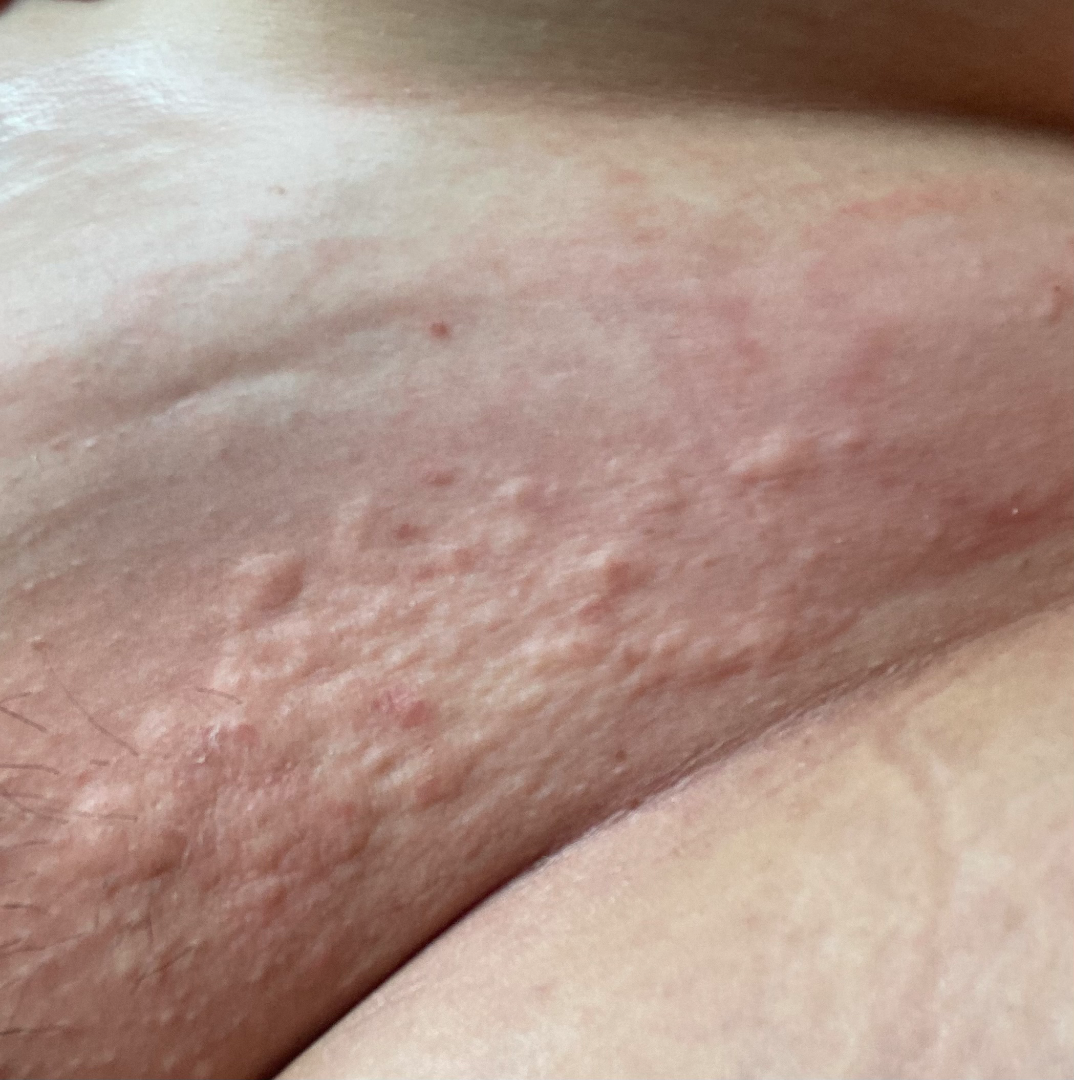The condition could not be reliably identified from the image. Texture is reported as raised or bumpy. Self-categorized by the patient as a rash. The patient reports enlargement and itching. Skin tone: Fitzpatrick skin type IV. This image was taken at an angle.